Located on the leg. The photograph was taken at an angle.
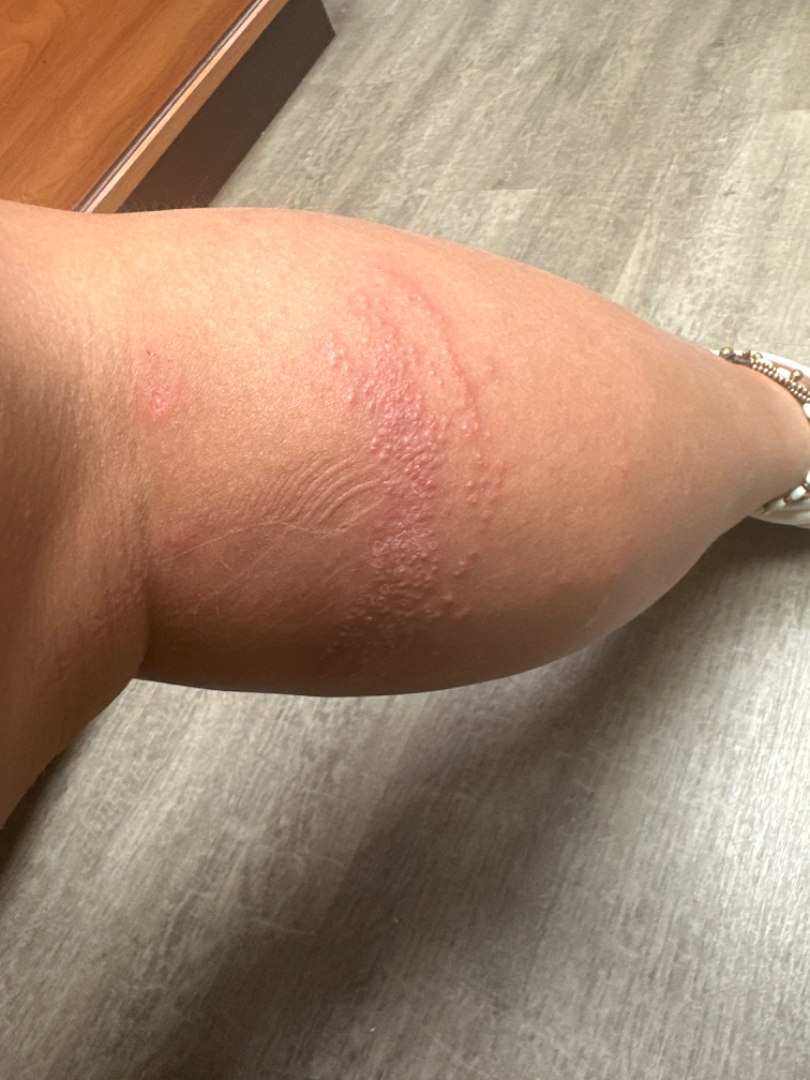The dermatologist could not determine a likely condition from the photograph alone.